The affected area is the front of the torso, arm and leg · the photograph was taken at an angle · female patient, age 30–39 — 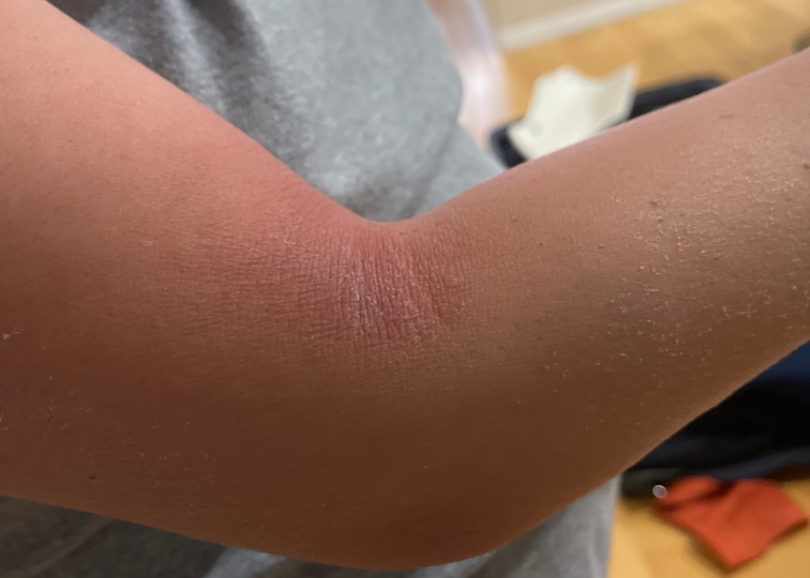The reviewing panel's impression was: the favored diagnosis is Eczema.